A female subject in their 70s; a clinical close-up photograph of a skin lesion:
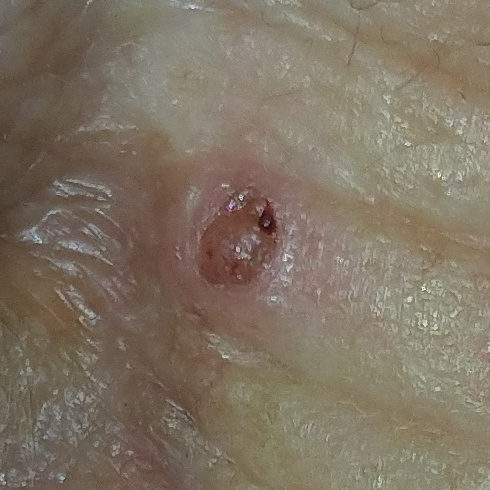location: the nose; reported symptoms: growth, itching, elevation, bleeding; pathology: basal cell carcinoma (biopsy-proven).